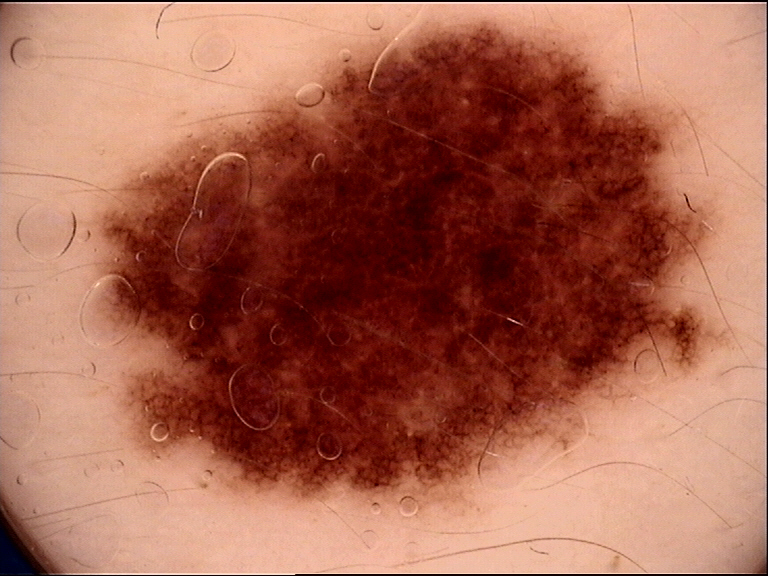Diagnosed as a benign lesion — a dysplastic junctional nevus.